A dermatoscopic image of a skin lesion: 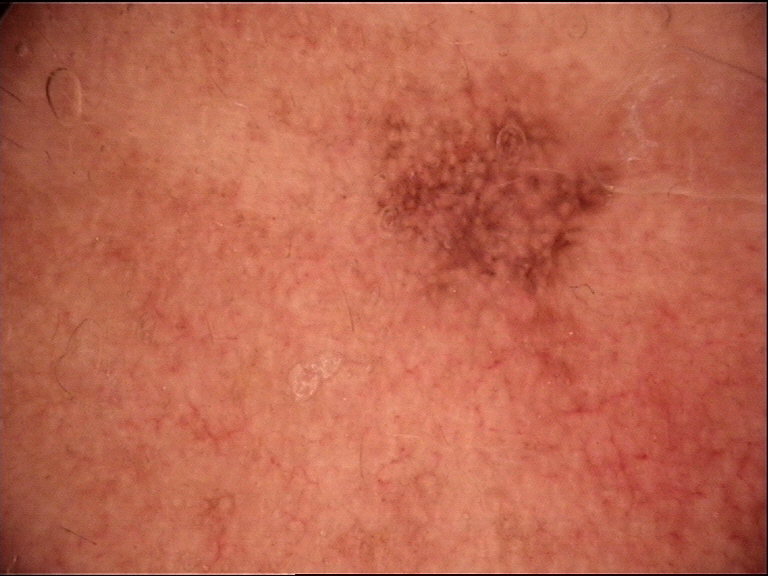Diagnosed as a keratinocytic lesion — an actinic keratosis.